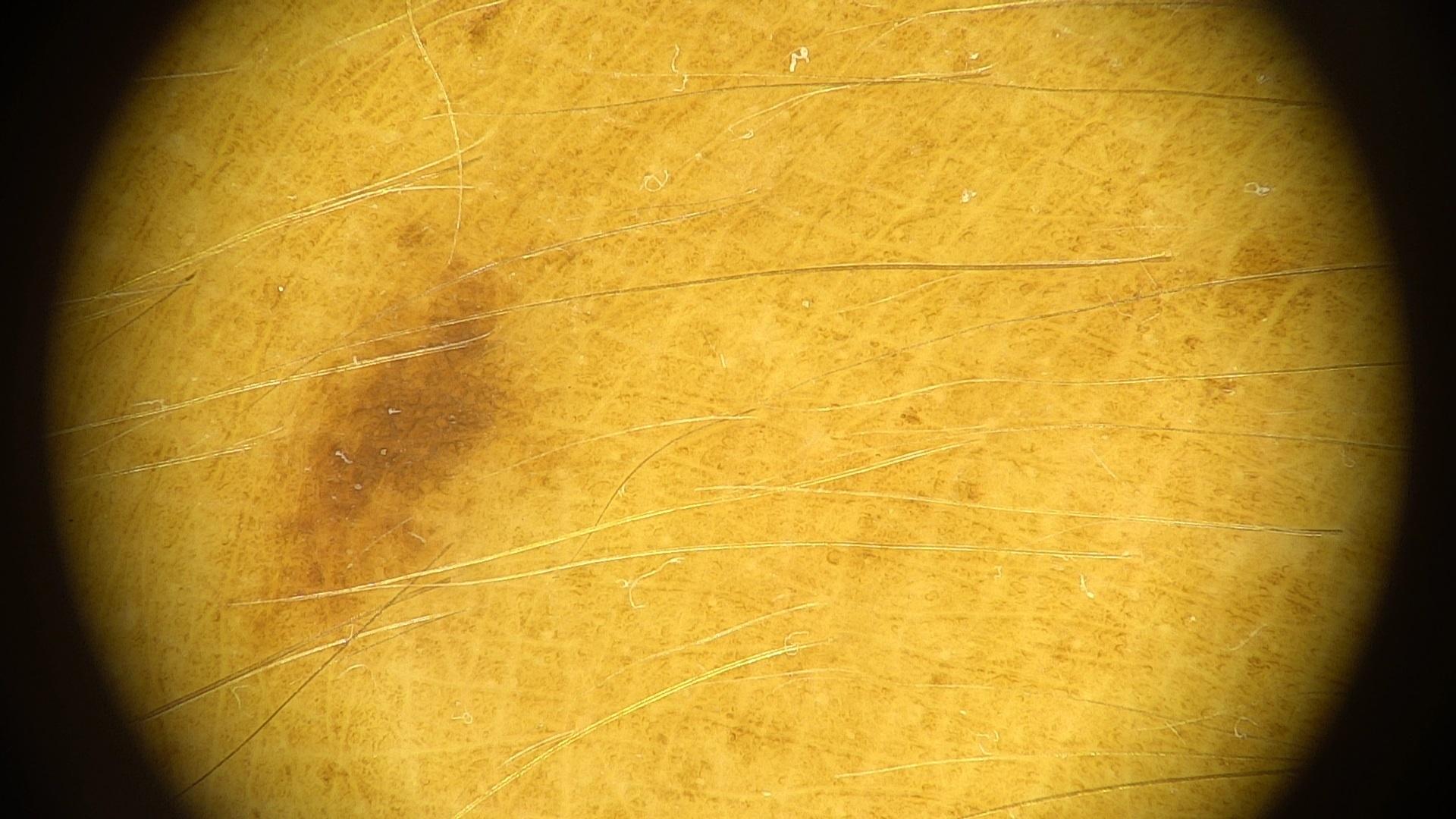A dermoscopic close-up of a skin lesion.
A female patient aged 33 to 37.
The patient is Fitzpatrick II.
The lesion is on a lower extremity.
The clinical assessment was a nevus.